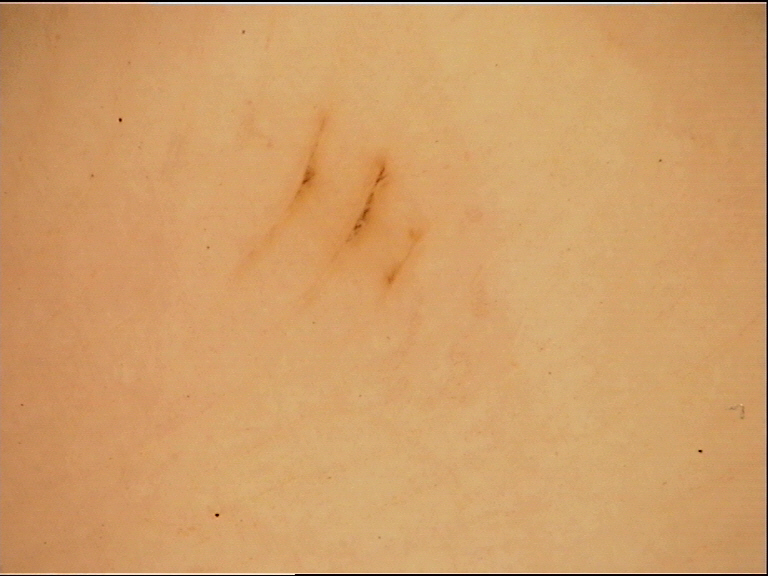Diagnosed as an acral junctional nevus.